Collected as part of a research study, without a referral diagnosis; a moderate number of moles by the patient's own estimate; a female subject 50 years old; the patient says their skin reddens painfully with sun exposure; by self-report, no family history of skin cancer and no personal history of cancer; a dermatoscopic image of a skin lesion: 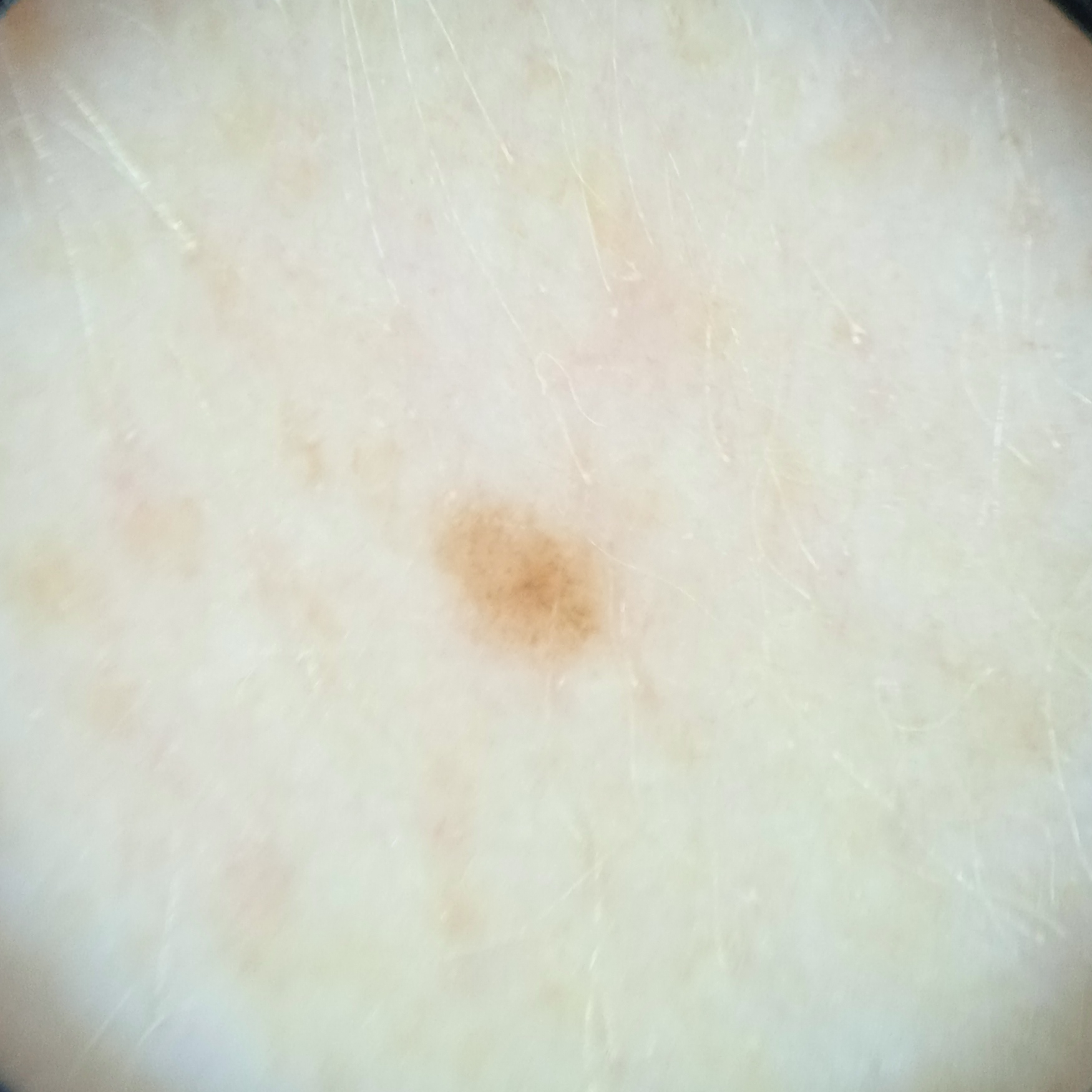The lesion is located on an arm. The lesion is about 2 mm across. The lesion was assessed as a melanocytic nevus.